The photograph is a close-up of the affected area · texture is reported as raised or bumpy · the front of the torso, top or side of the foot, back of the torso, arm, leg and back of the hand are involved · self-categorized by the patient as a rash · present for one to four weeks · male patient, age 18–29 · reported lesion symptoms include itching, enlargement, bothersome appearance and darkening — 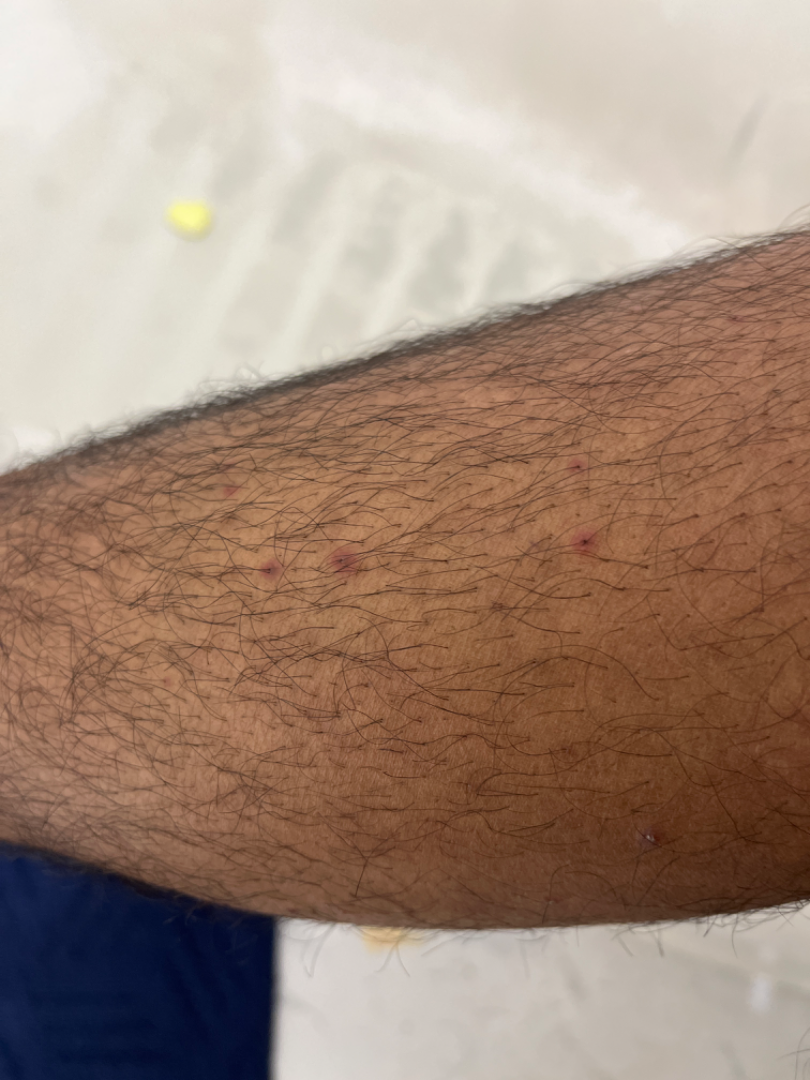Three dermatologists each reviewed the case: most consistent with Folliculitis; less probable is Psoriasis; a more distant consideration is Perifolliculitis.